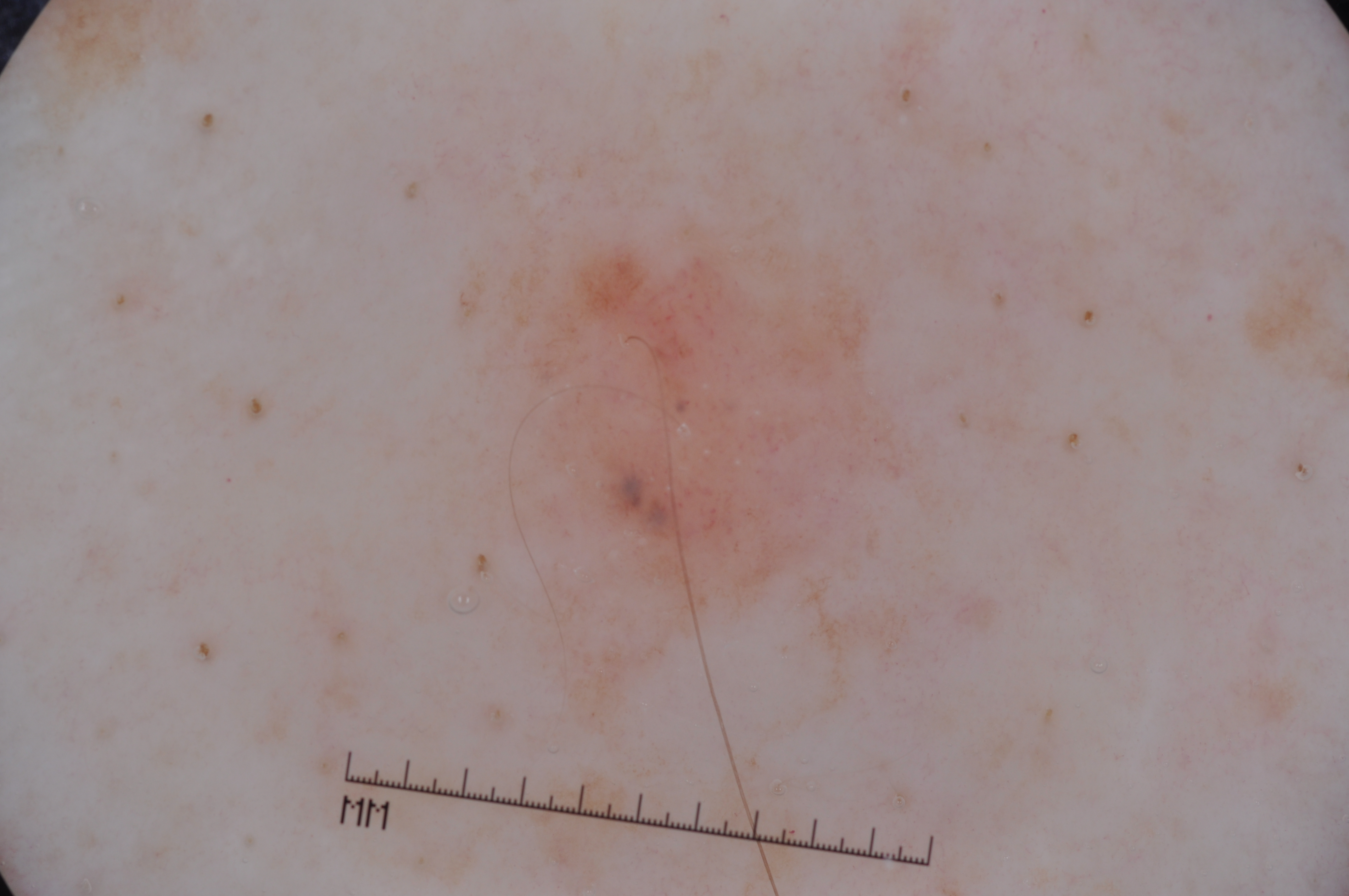Case summary:
- patient · male, roughly 55 years of age
- image type · dermoscopy of a skin lesion
- bounding box · [416,165,918,743]
- dermoscopic findings · milia-like cysts; absent: negative network, streaks, and pigment network
- assessment · a melanocytic nevus